Dermoscopy of a skin lesion.
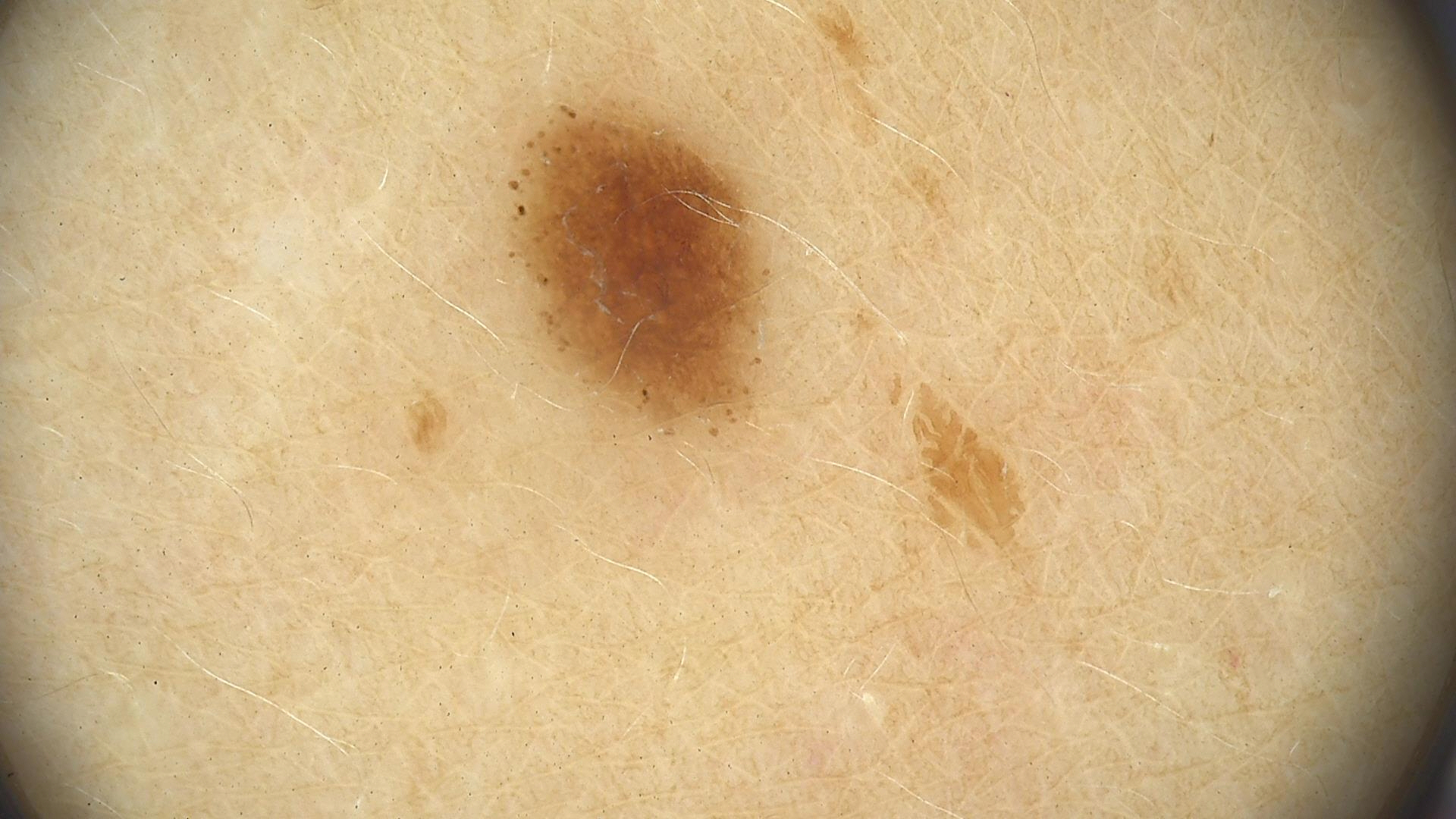diagnostic label: dysplastic junctional nevus (expert consensus).